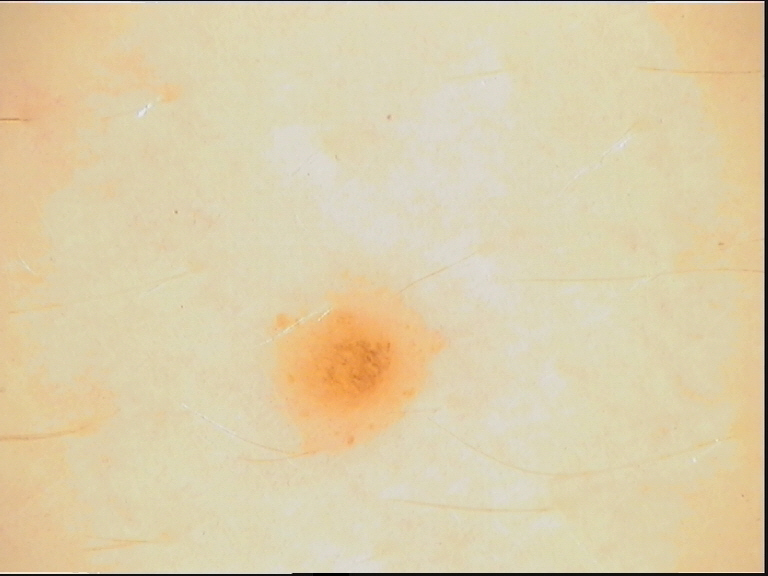Q: What was the diagnostic impression?
A: junctional nevus (expert consensus)